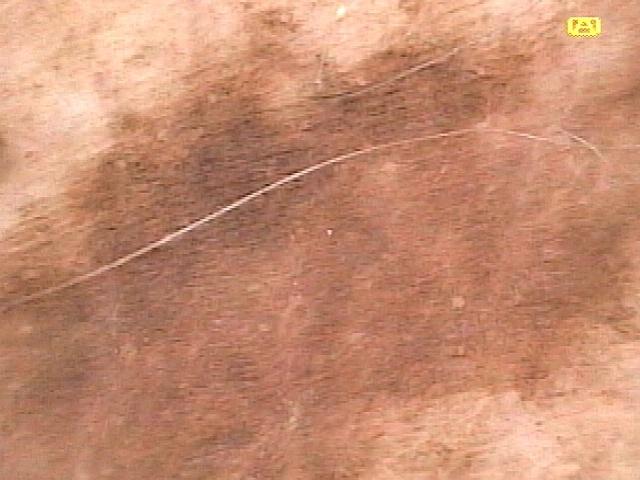Summary:
Recorded as Fitzpatrick I. A dermatoscopic image of a skin lesion. A female patient about 80 years old. The lesion was found on an upper extremity.
Conclusion:
Confirmed on histopathology as a malignant lesion — a melanoma.